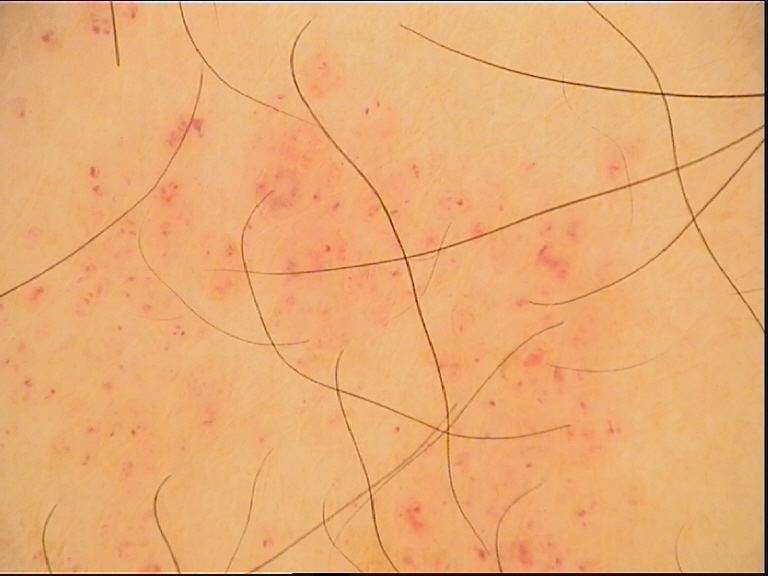image type=dermoscopy
label=hemangioma (expert consensus)